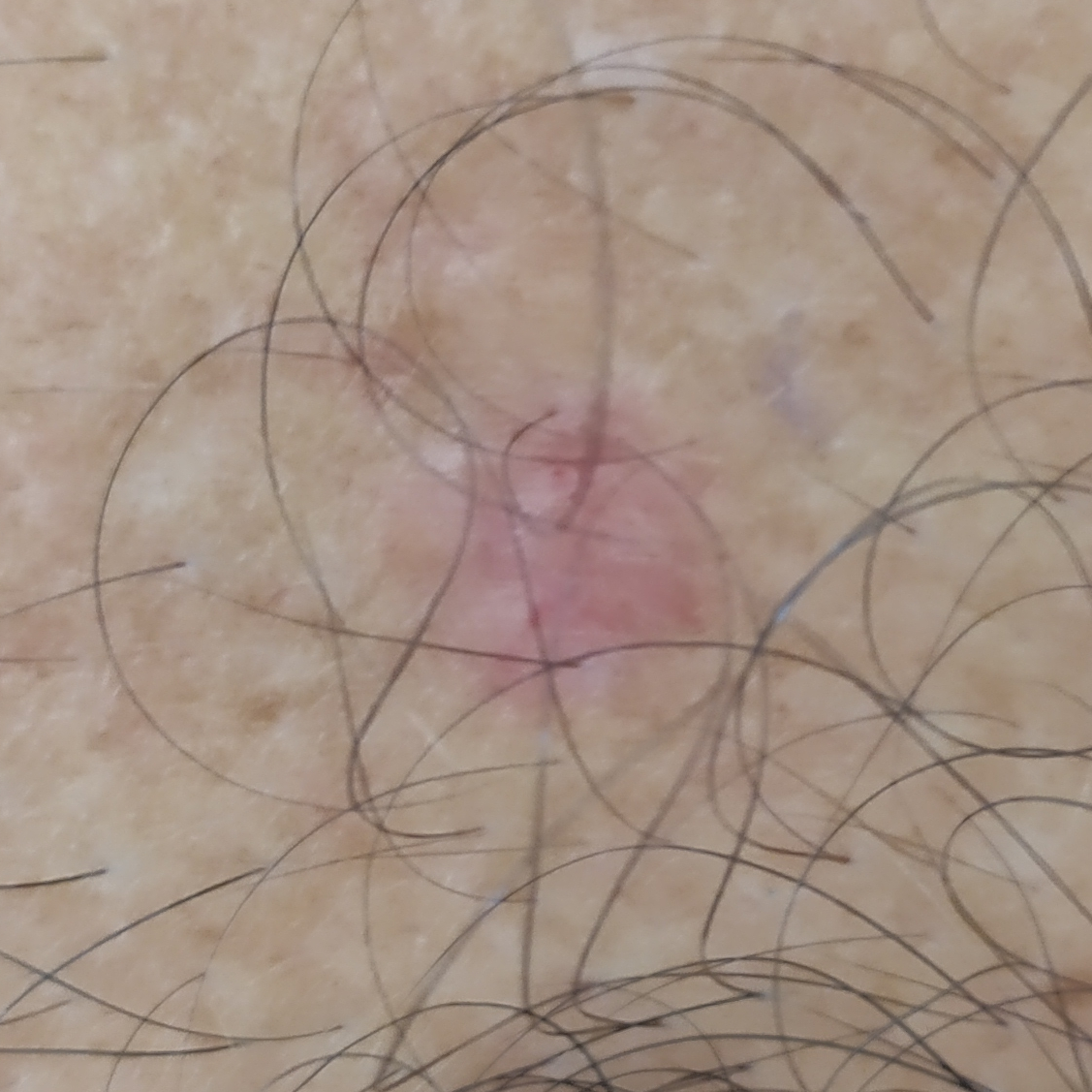Findings:
The patient is skin type III. A male subject aged 51. By the patient's account, the lesion is elevated.
Conclusion:
Histopathologically confirmed as a basal cell carcinoma.